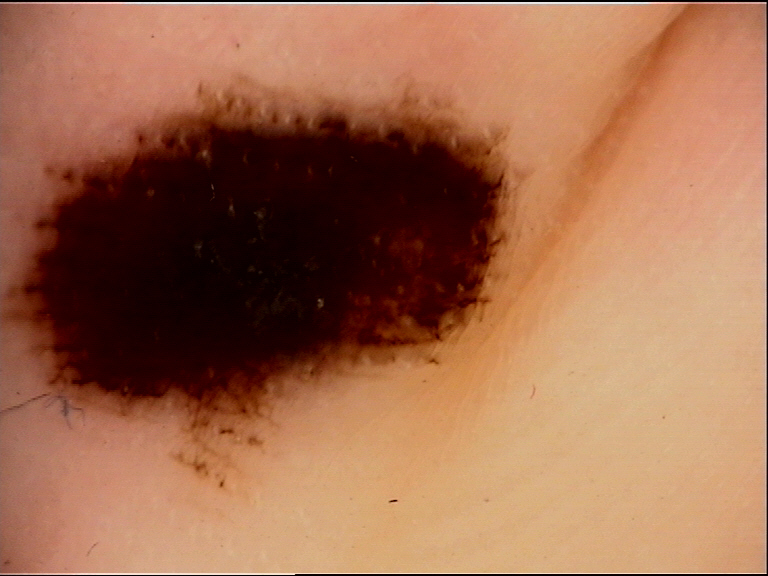A dermoscopic photograph of a skin lesion. Classified as an acral dysplastic junctional nevus.